A dermoscopy image of a single skin lesion.
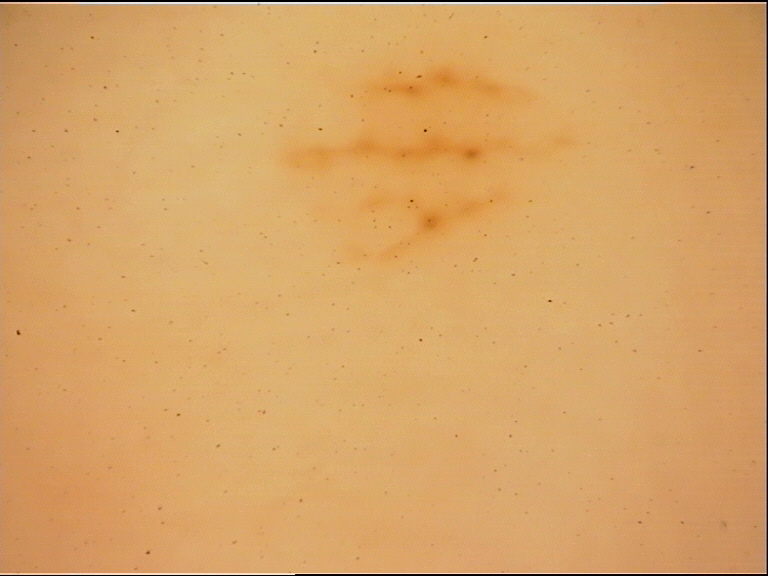lesion type: banal | class: acral junctional nevus (expert consensus).